The head or neck, front of the torso, back of the torso, back of the hand, top or side of the foot and arm are involved. This is a close-up image. The patient is male: 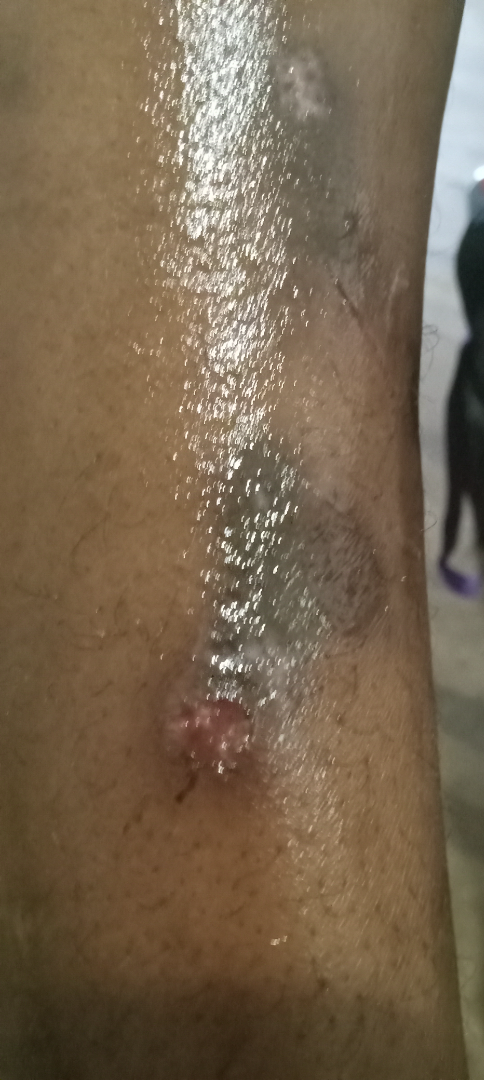Notes:
* assessment — indeterminate